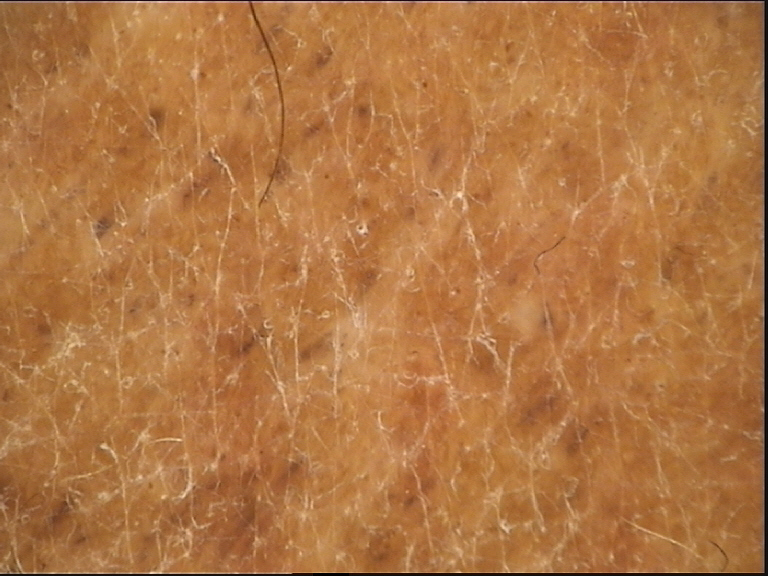| key | value |
|---|---|
| image | dermoscopy |
| classification | banal |
| label | congenital compound nevus (expert consensus) |